A dermatoscopic image of a skin lesion.
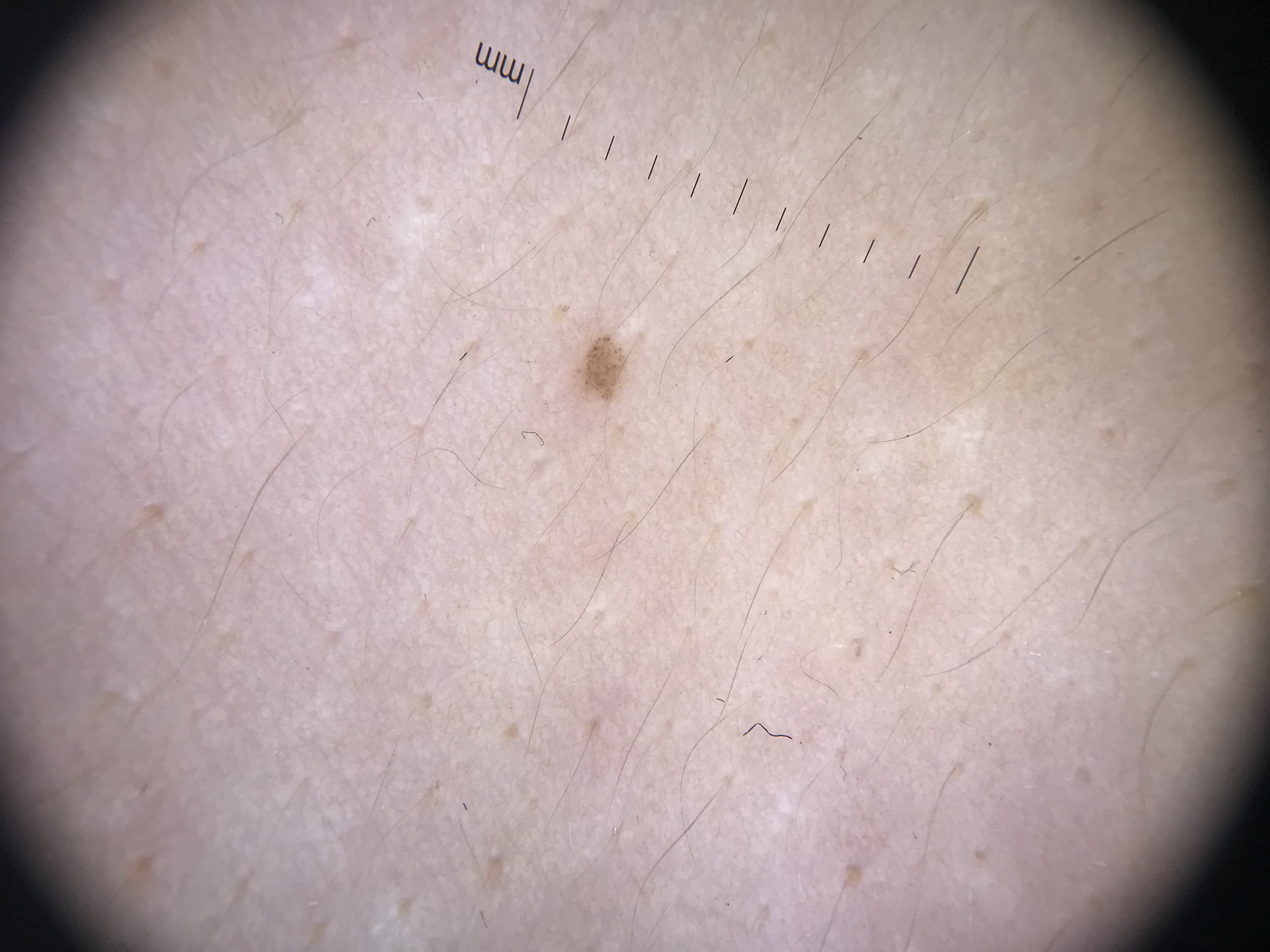This is a banal lesion. Consistent with a junctional nevus.